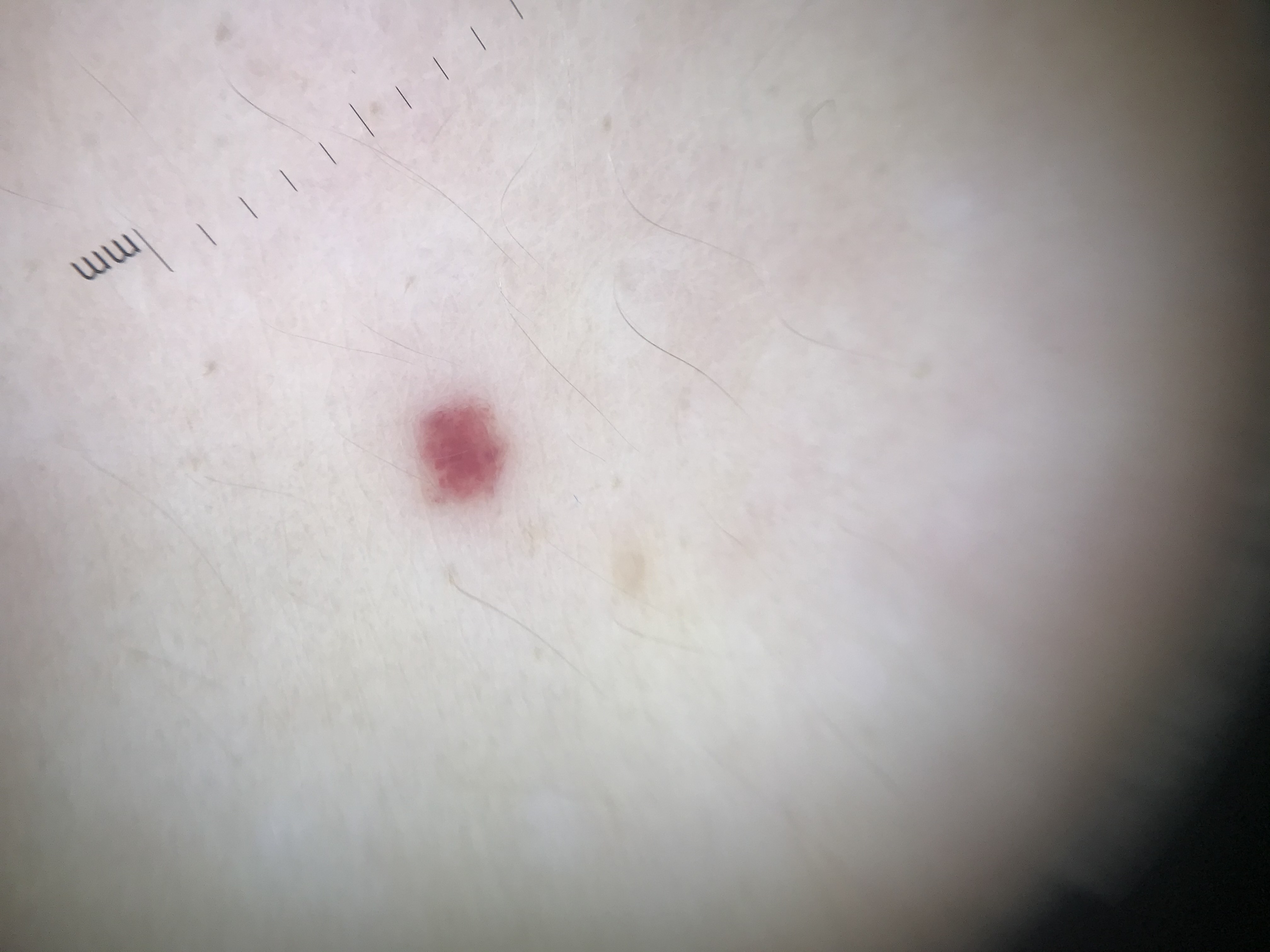image=dermoscopy
category=vascular
diagnostic label=hemangioma (expert consensus)